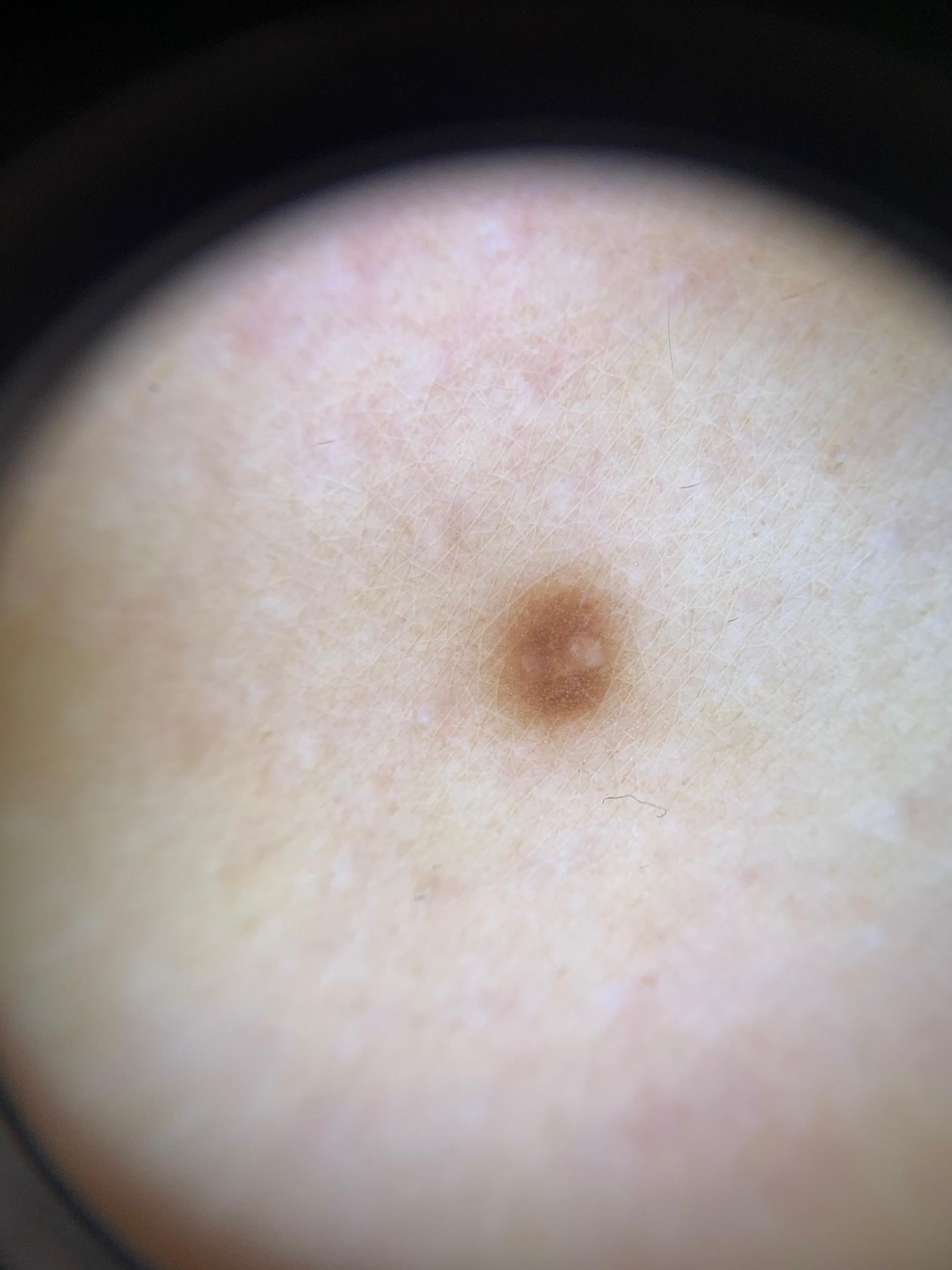Q: What is the diagnosis?
A: Dermatofibroma